A dermoscopic view of a skin lesion. The subject is a female aged approximately 75:
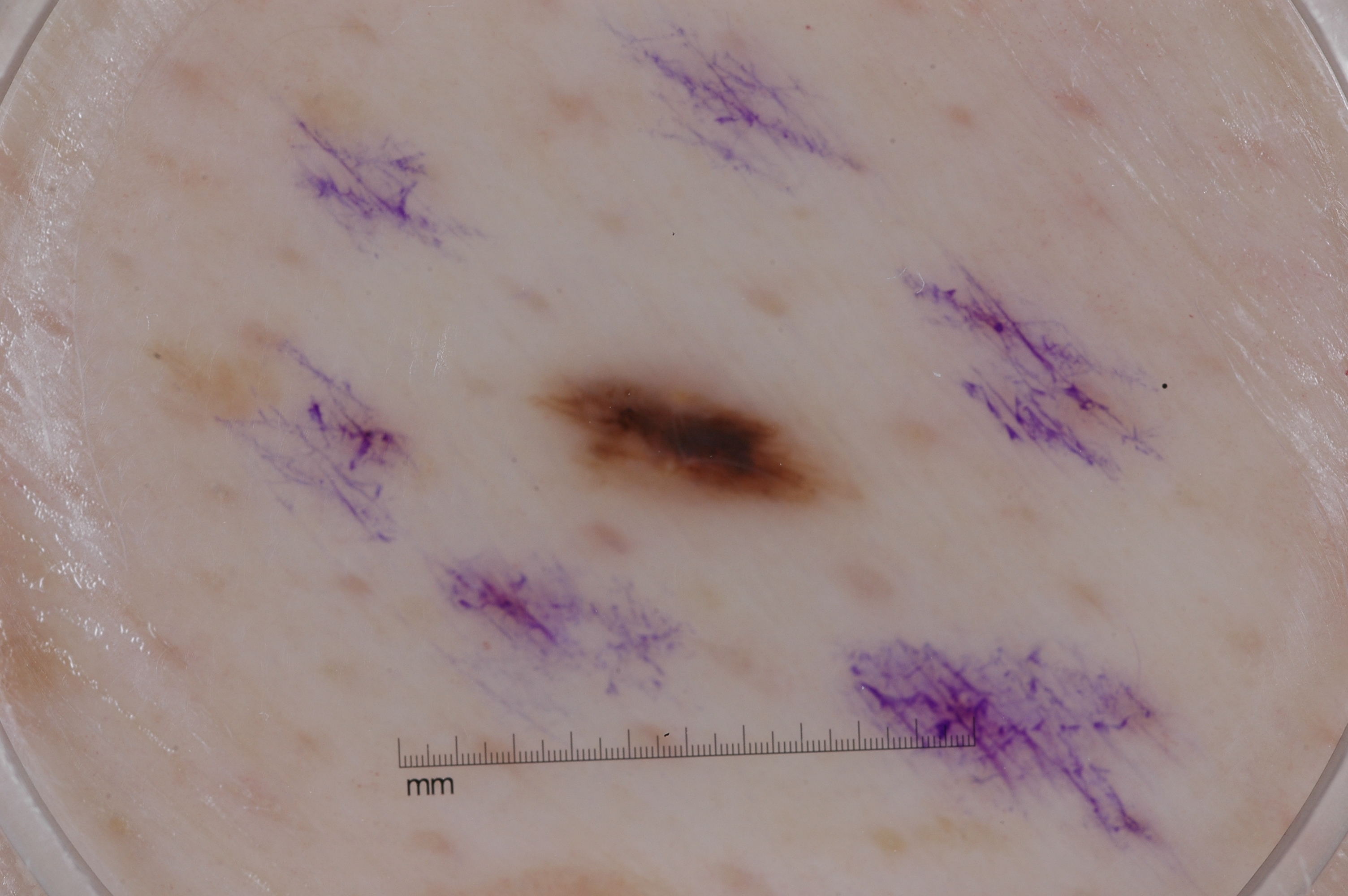dermoscopic features not present: pigment network, milia-like cysts, streaks, and negative network
bounding box: left=519, top=350, right=863, bottom=536
extent: ~3% of the field
impression: a melanocytic nevus